The photo was captured at an angle, the back of the hand is involved.
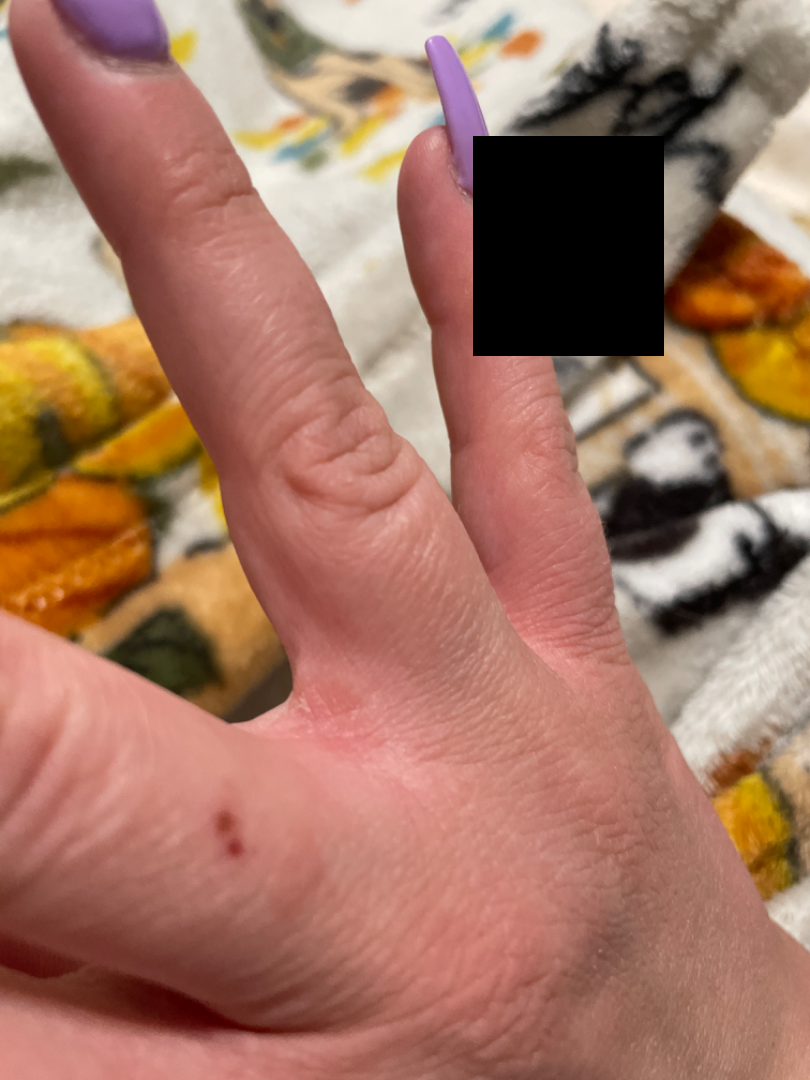Notes:
• patient describes the issue as — a rash
• reported symptoms — burning and itching
• present for — one to four weeks
• impression — Irritant Contact Dermatitis (weight 1.00)